A close-up photograph:
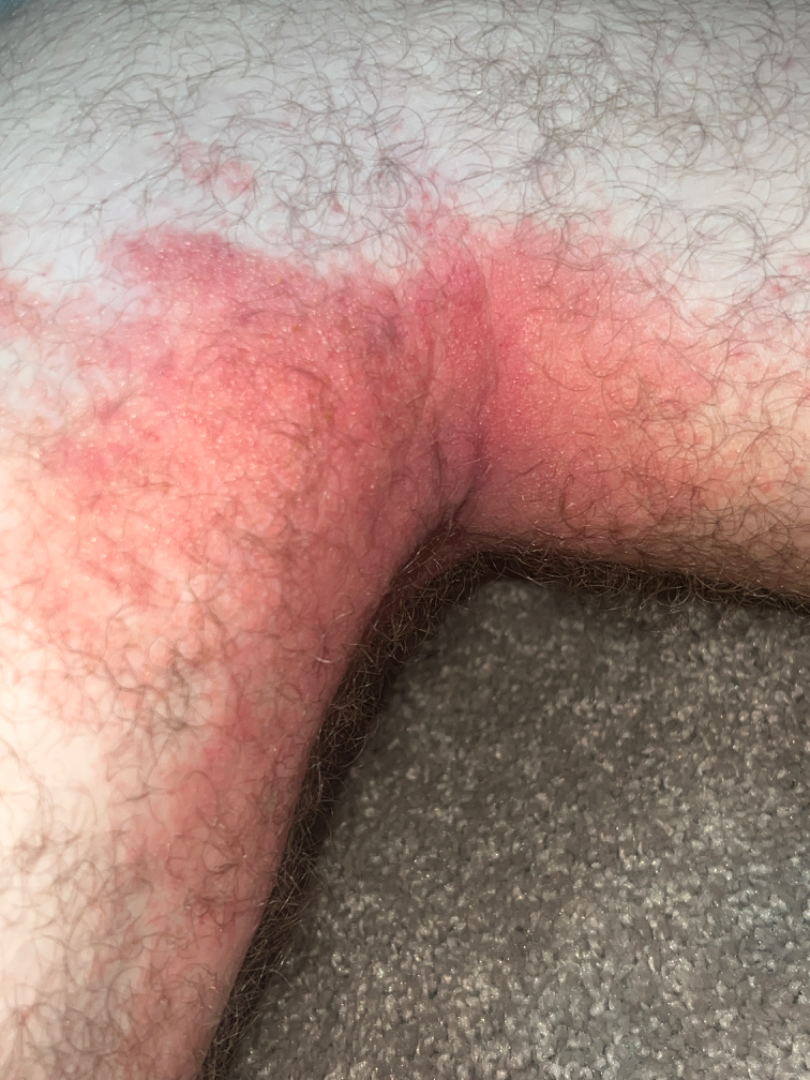Notes:
– diagnostic considerations · favoring Allergic Contact Dermatitis; the differential also includes Eczema